The patient reports enlargement and bothersome appearance, the patient reported no systemic symptoms, the photograph is a close-up of the affected area, the patient reports the lesion is fluid-filled and raised or bumpy, self-categorized by the patient as acne, the lesion involves the arm, present for one to four weeks.
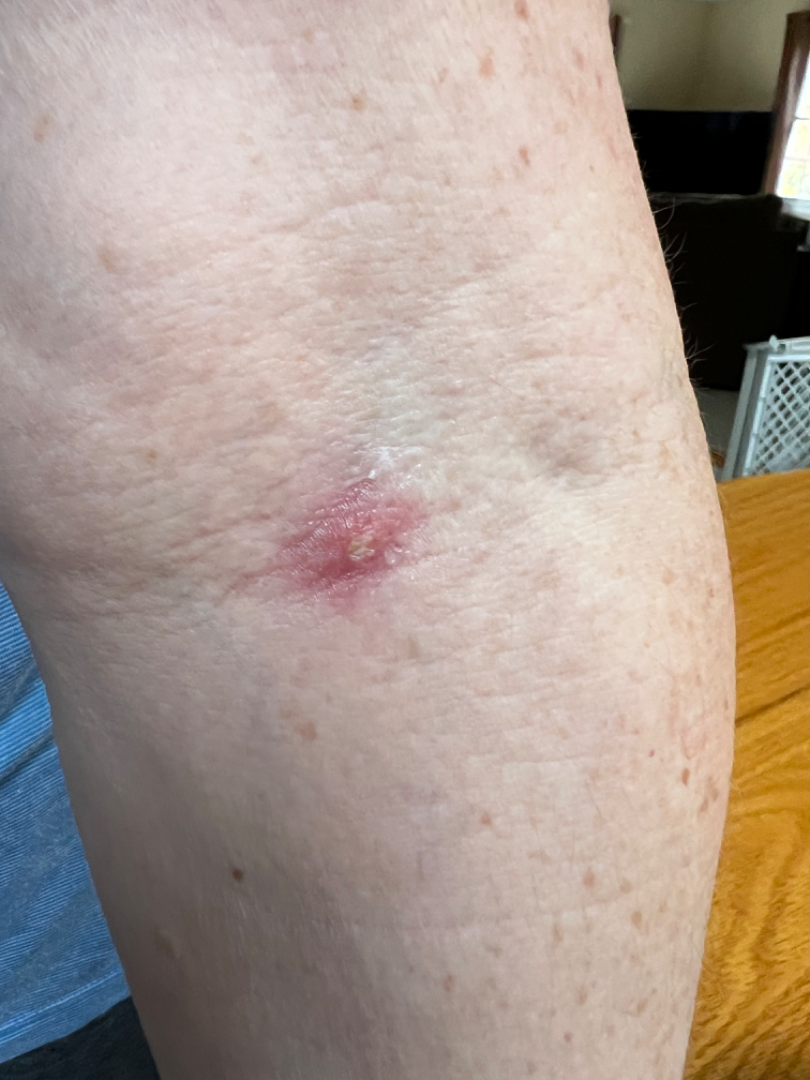Impression:
On dermatologist assessment of the image, Cyst (considered); Furuncle (considered).